A female subject age 48 · collected as part of a research study, without a referral diagnosis.
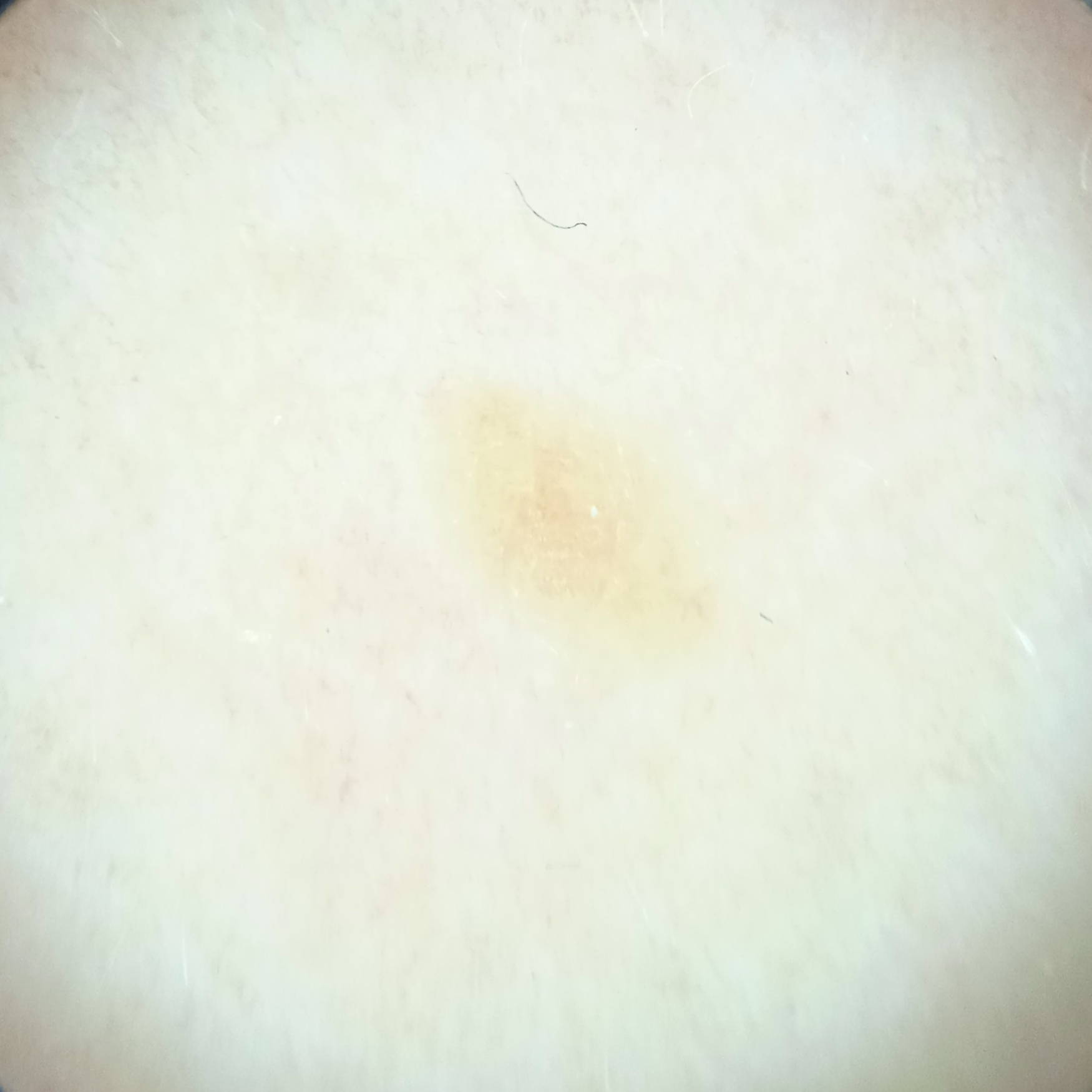{
  "lesion_location": "the back",
  "diagnosis": {
    "name": "seborrheic keratosis",
    "malignancy": "benign"
  }
}